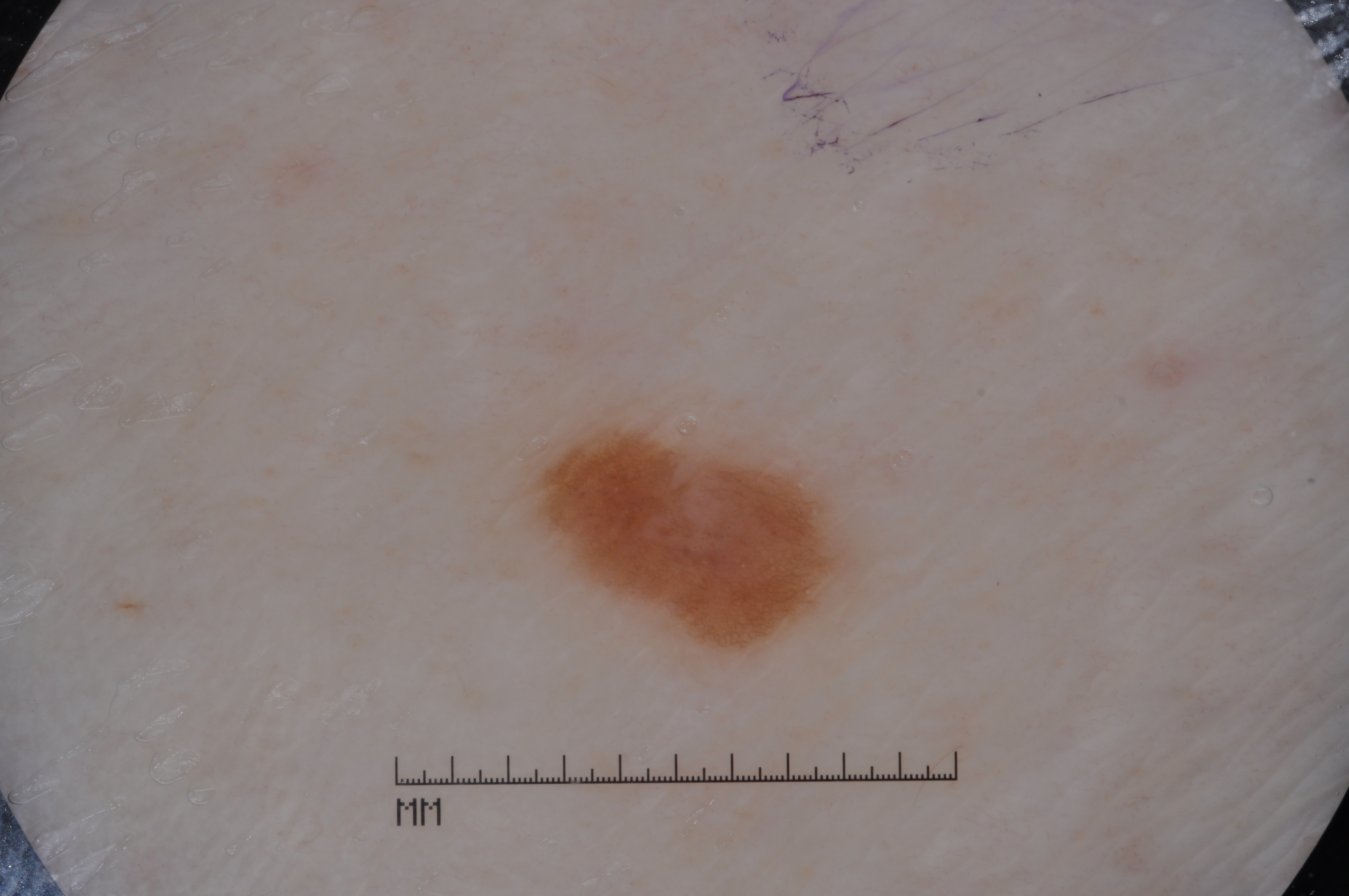A male subject approximately 75 years of age.
A skin lesion imaged with a dermatoscope.
The visible lesion spans left=520, top=419, right=858, bottom=658.
A small lesion within a wider field of skin.
Dermoscopic review identifies pigment network; no negative network, milia-like cysts, or streaks.
The lesion was assessed as a melanocytic nevus.